The contributor is female; symptoms reported: bothersome appearance; the patient notes the lesion is rough or flaky and raised or bumpy; the patient notes the condition has been present for more than one year; self-categorized by the patient as a hair problem; the photo was captured at a distance; the arm and leg are involved.
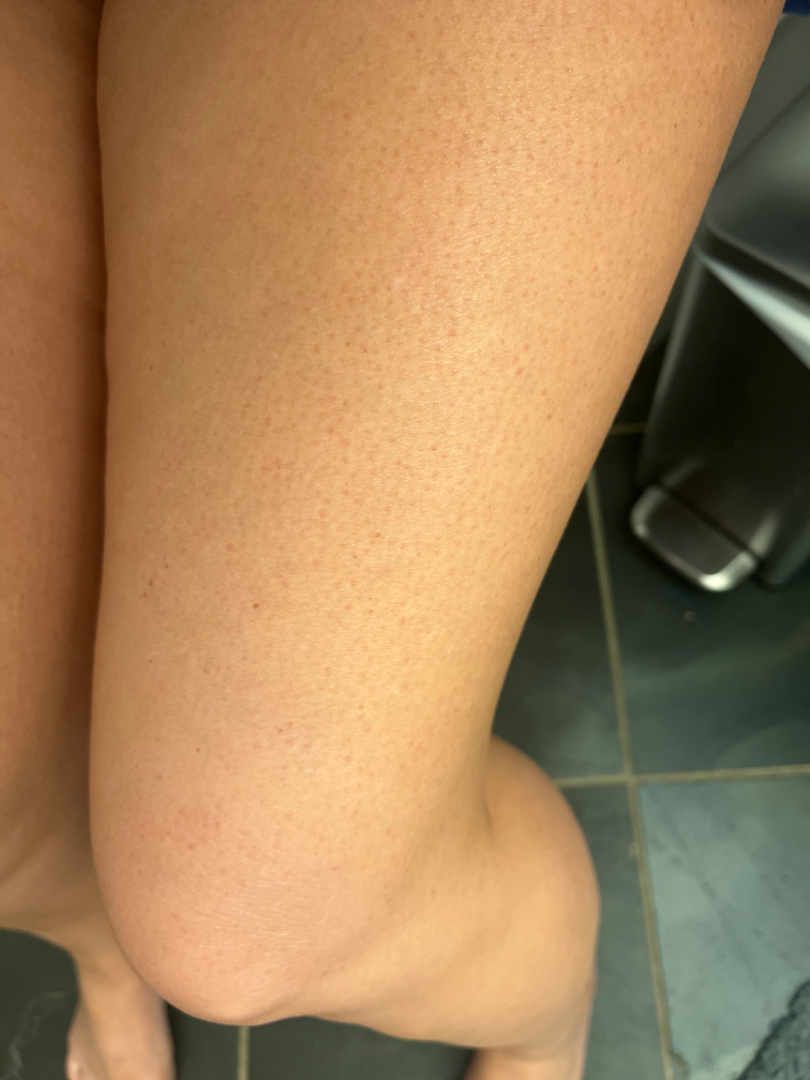Findings:
The reviewing dermatologists' impression was: in keeping with Keratosis pilaris.